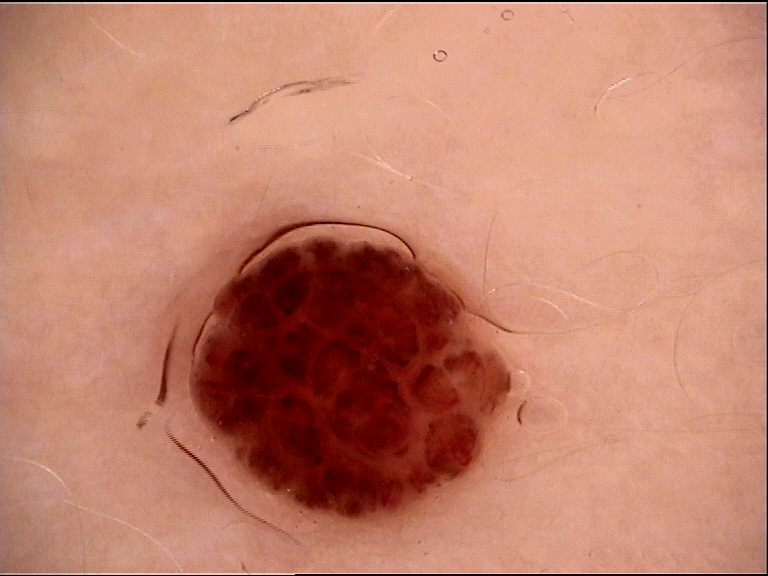diagnostic label: compound nevus (expert consensus)